A skin lesion imaged with a dermatoscope.
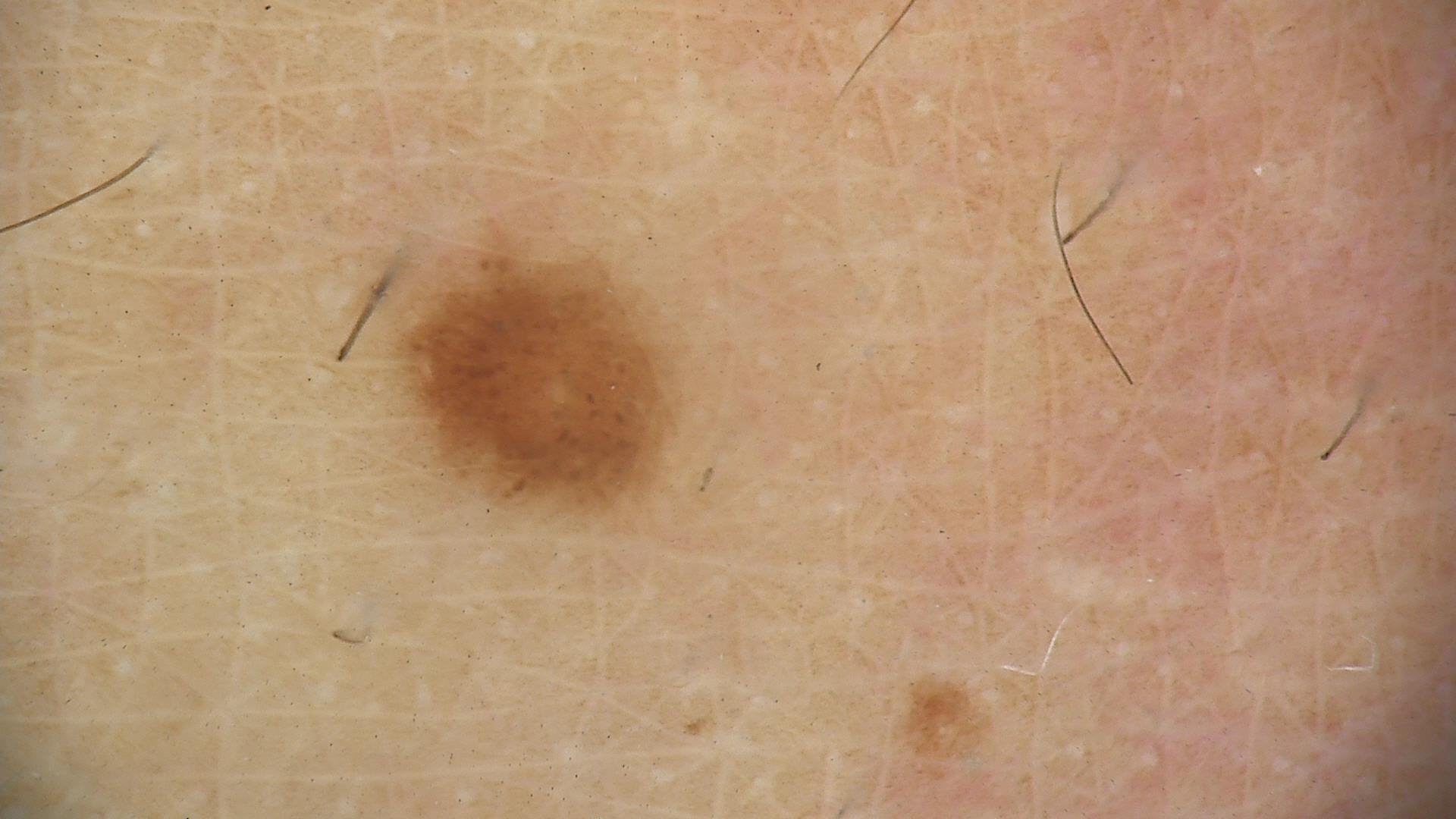{
  "diagnosis": {
    "name": "dysplastic junctional nevus",
    "code": "jd",
    "malignancy": "benign",
    "super_class": "melanocytic",
    "confirmation": "expert consensus"
  }
}